This image was taken at an angle; the subject is 40–49, female; the lesion involves the leg.
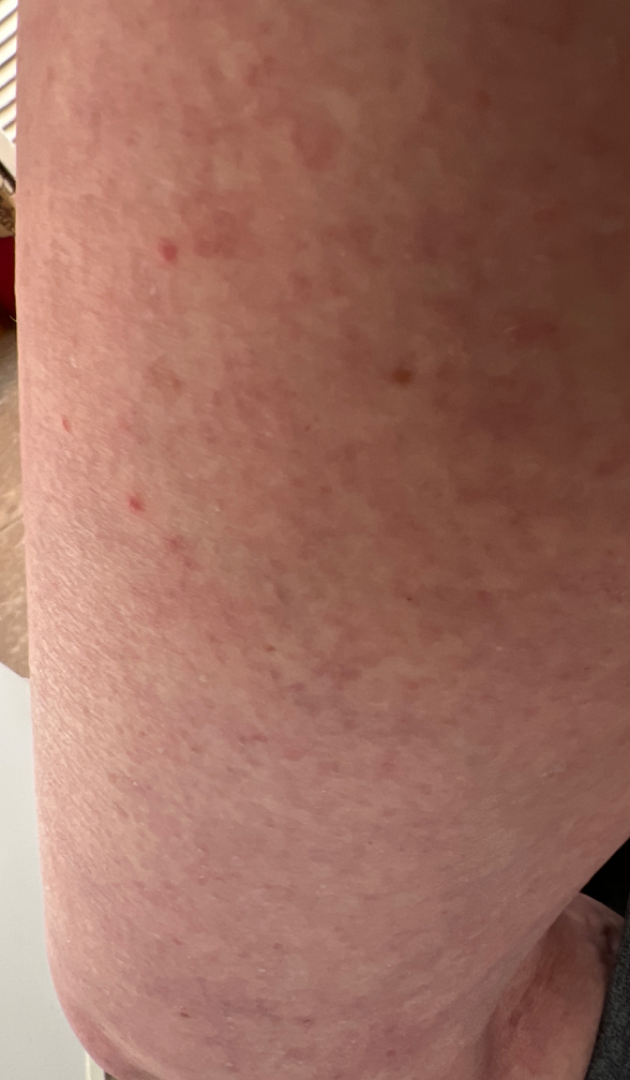– assessment: indeterminate from the photograph
– present for: one to four weeks
– lesion texture: raised or bumpy
– systemic symptoms: fever, fatigue and joint pain
– lesion symptoms: pain
– skin tone: FST II; non-clinician graders estimated 2 on the Monk skin tone scale